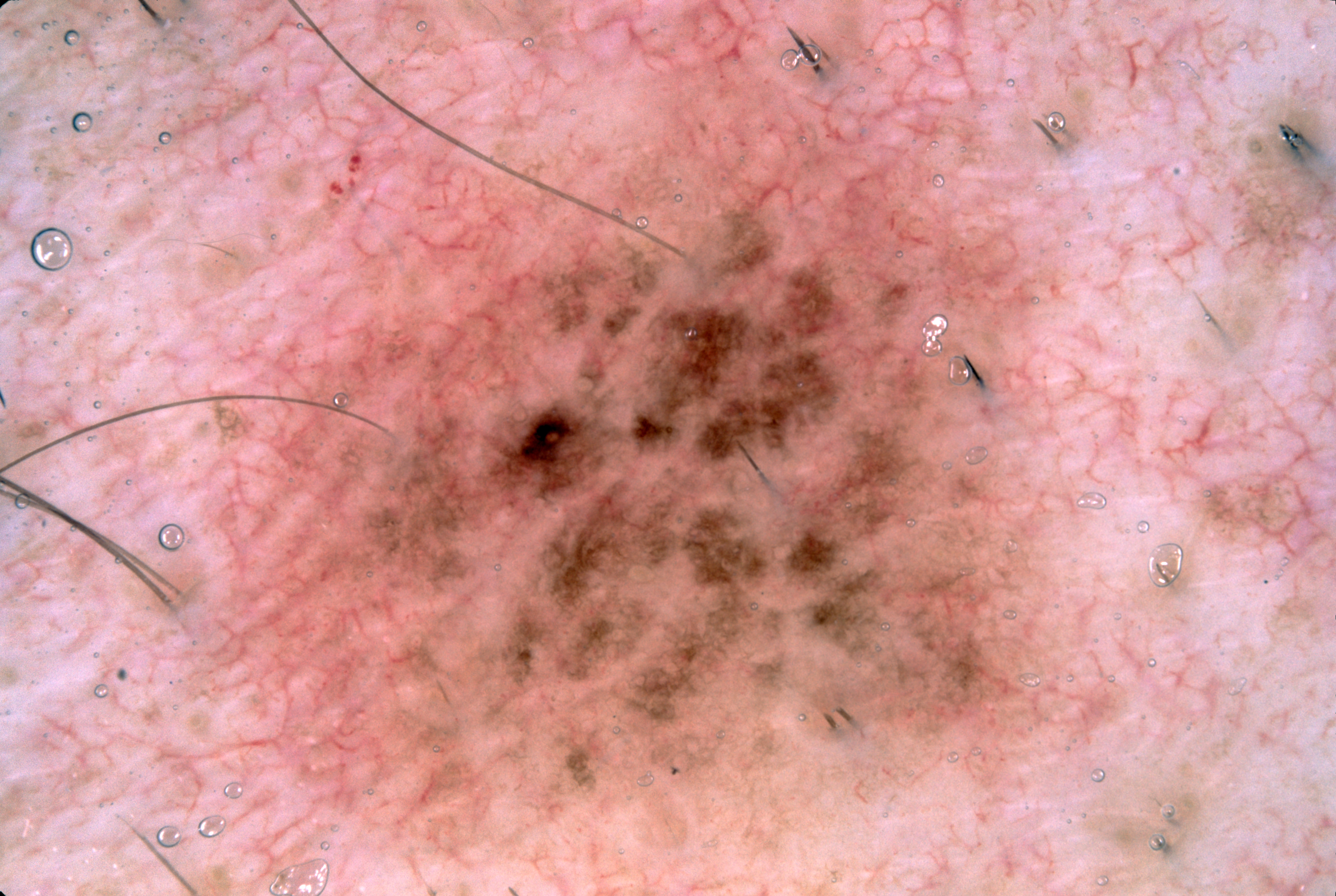subject = male | imaging = dermatoscopic image of a skin lesion | size = large | dermoscopic findings = pigment network; absent: streaks, milia-like cysts, and negative network | lesion bbox = (154, 5, 1201, 892) | impression = a melanocytic nevus, a benign skin lesion.